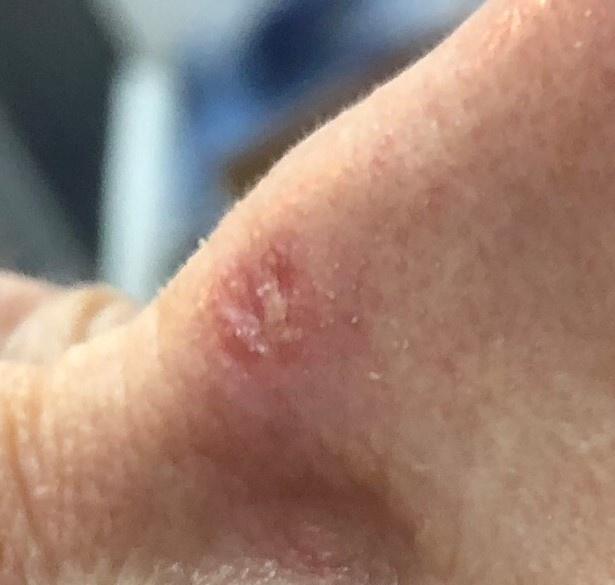Findings: A female patient aged 78-82. A clinical photograph showing a skin lesion in context. The lesion is on the head or neck. Conclusion: On biopsy, the diagnosis was a lesion of adnexal (follicular) origin — a basal cell carcinoma.